The lesion involves the palm and back of the hand · the contributor is 18–29, female · this is a close-up image · texture is reported as raised or bumpy and rough or flaky · the condition has been present for more than one year · reported lesion symptoms include itching, pain and burning:
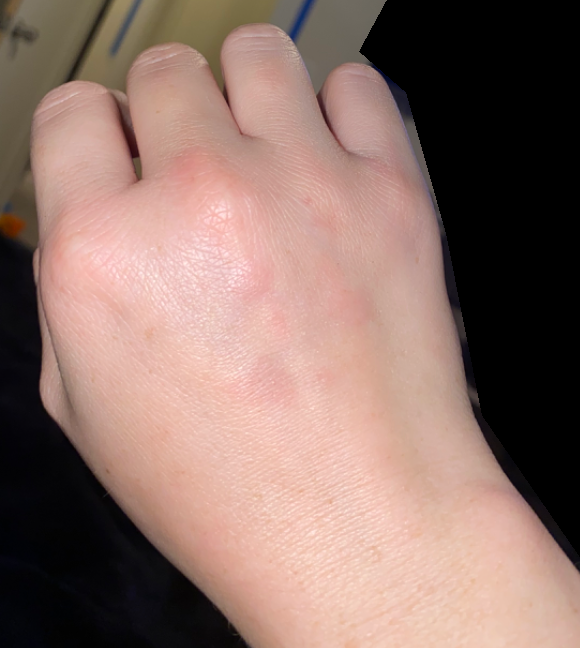Findings: On remote review of the image, most likely Granuloma annulare; a remote consideration is Insect Bite; less likely is Allergic Contact Dermatitis; less probable is Eczema.